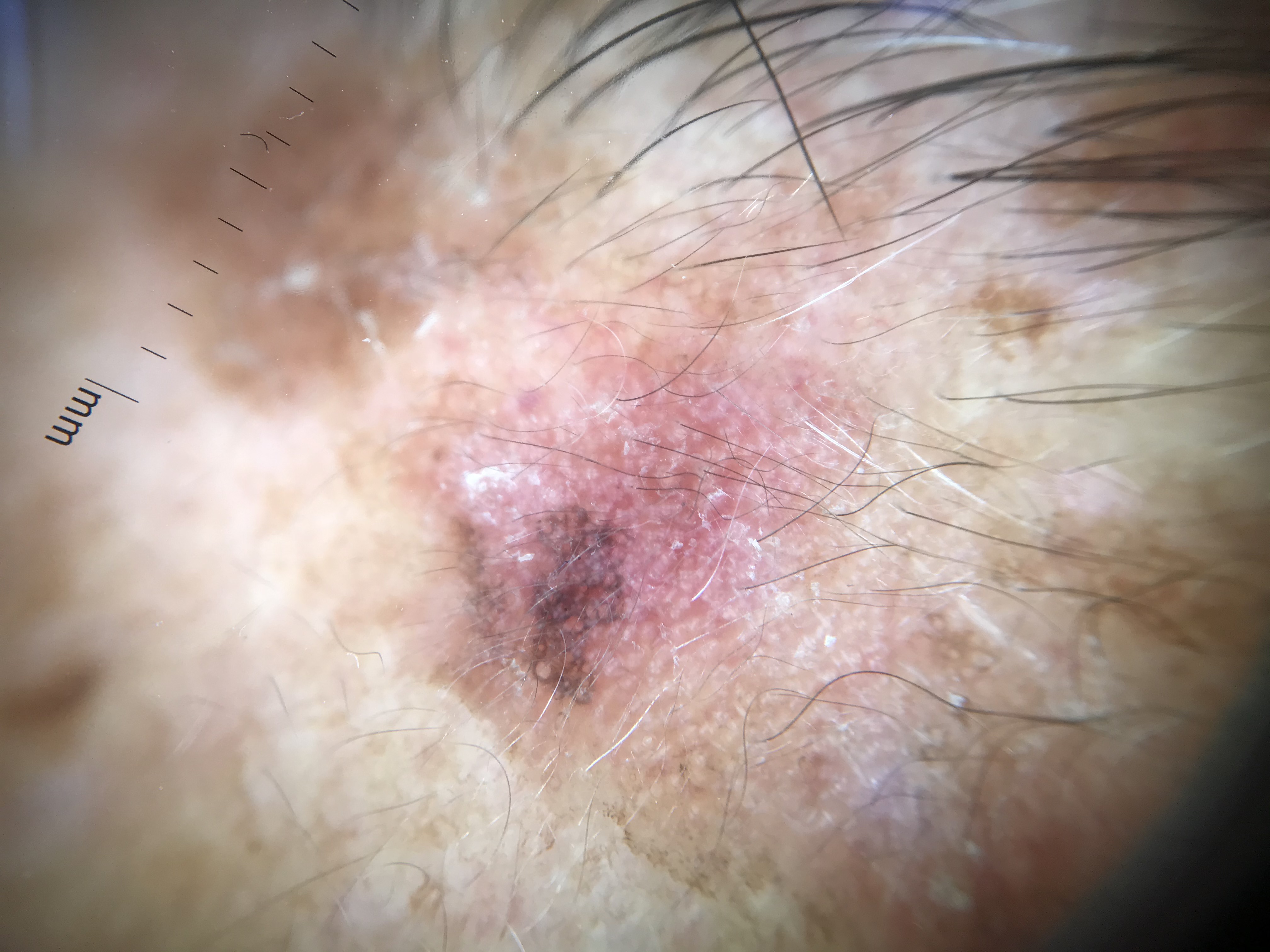assessment=actinic keratosis (expert consensus).